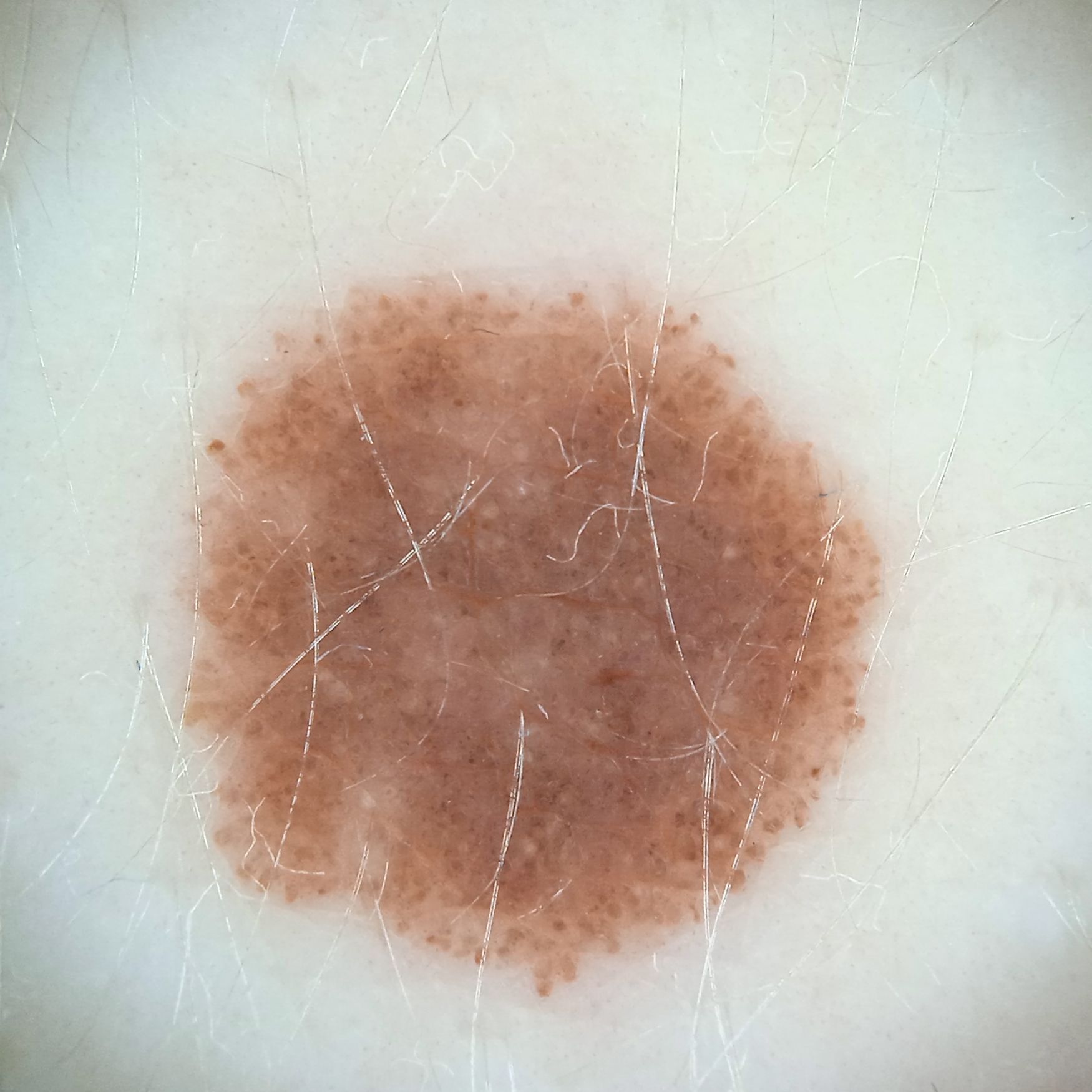Acquired for a research image collection, with no referral diagnosis. A female patient 26 years of age. A dermoscopic image of a skin lesion. Located on the back. Measuring roughly 9.1 mm. The diagnostic impression was a melanocytic nevus.